A dermoscopic image of a skin lesion — 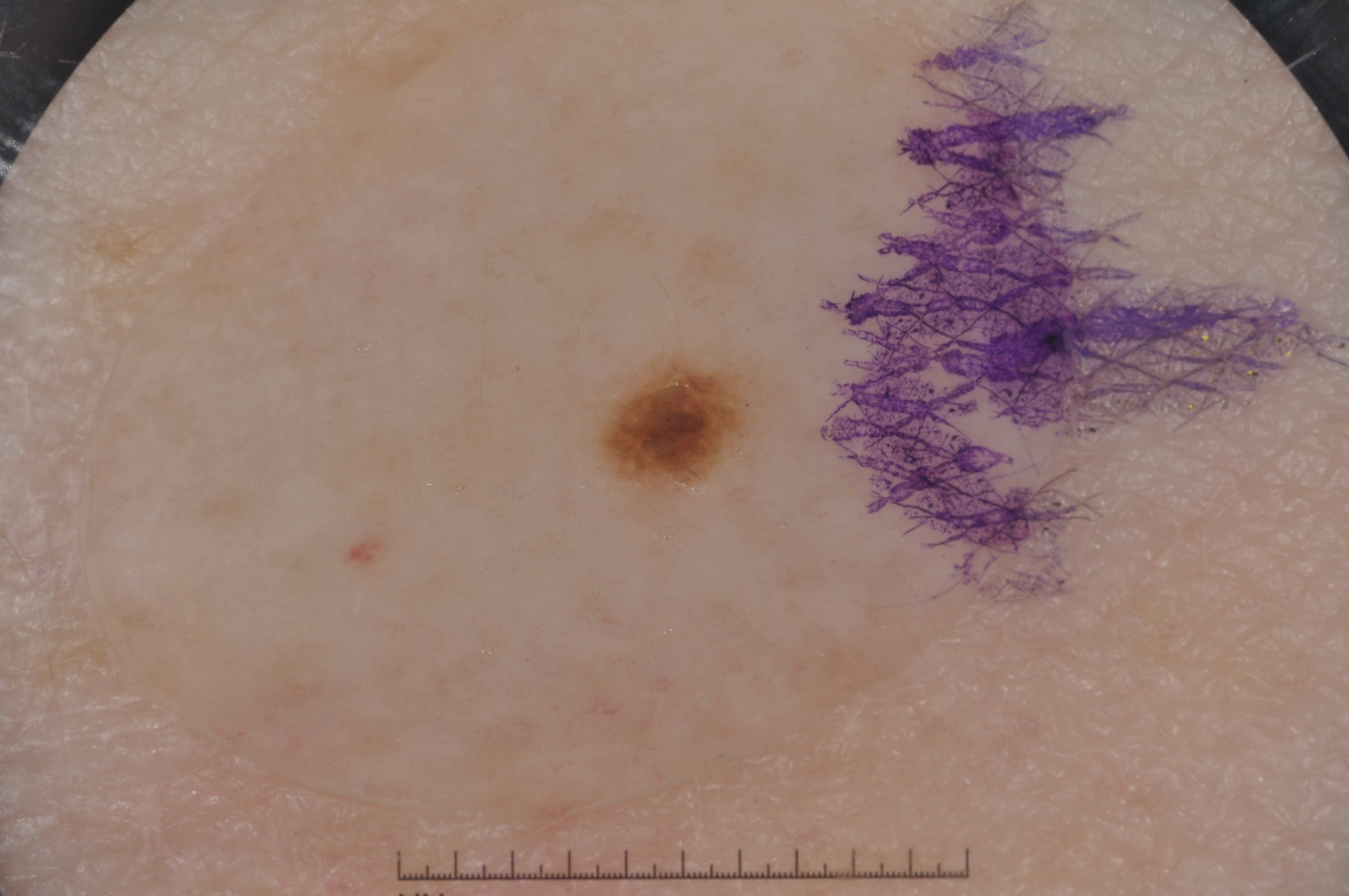dermoscopic features not present — negative network, pigment network, streaks, and milia-like cysts | location — bbox(601, 365, 748, 483) | impression — a melanocytic nevus, a benign lesion.